The leg is involved; the photograph was taken at a distance; the contributor is 18–29, male:
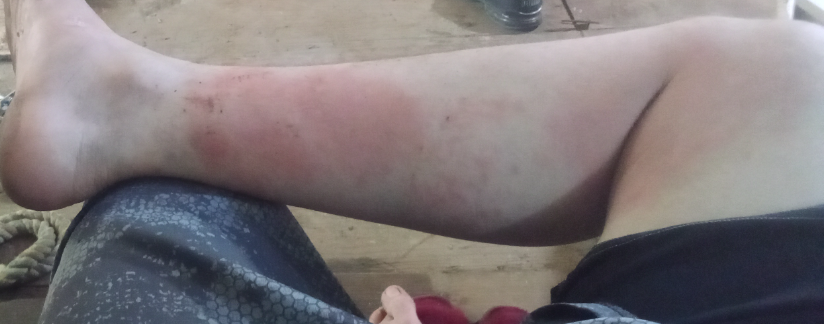assessment: could not be assessed.